A male subject 61 years of age:
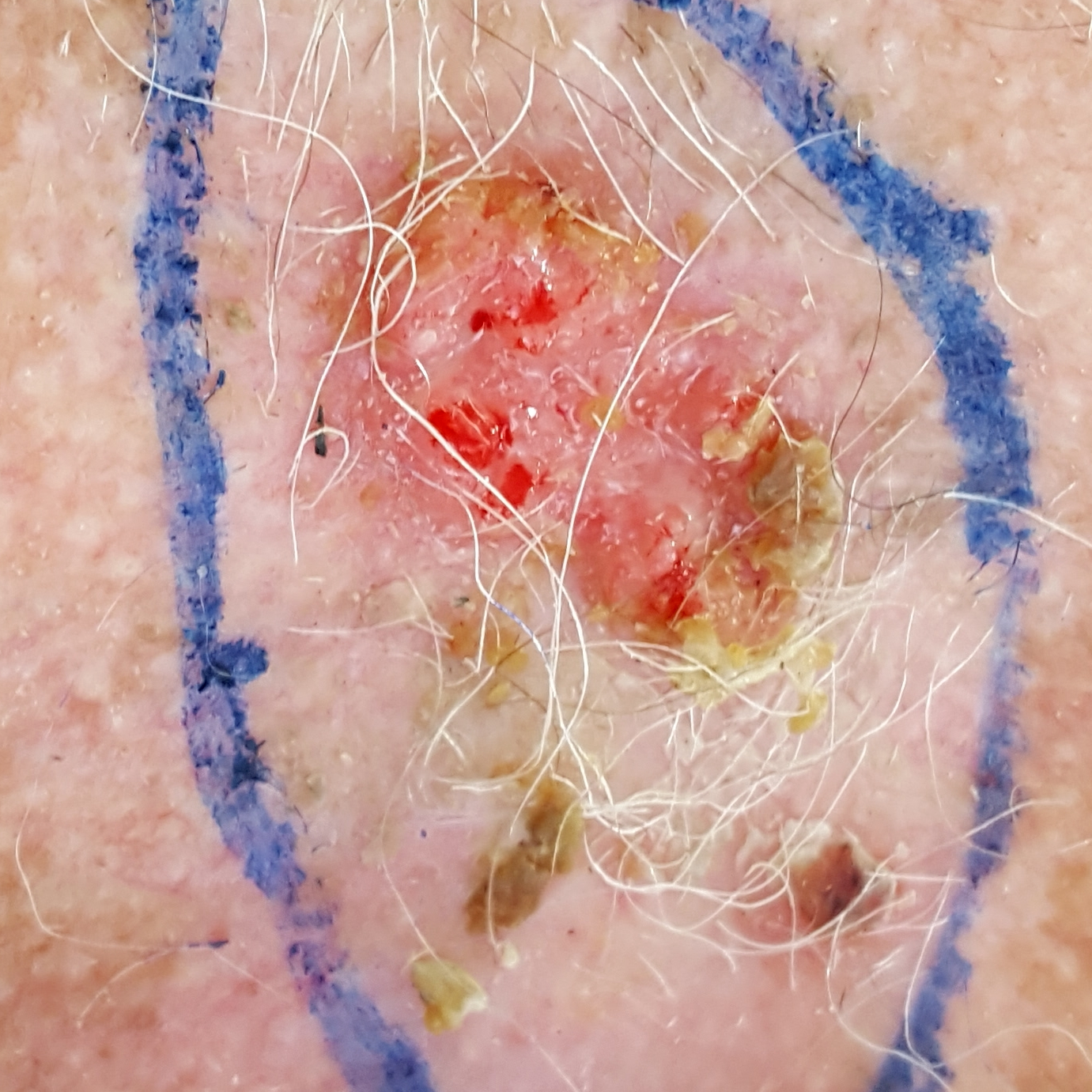Summary: The lesion is located on the chest. The patient reports that the lesion has bled, hurts, itches, and is elevated. Conclusion: On biopsy, the diagnosis was a basal cell carcinoma.